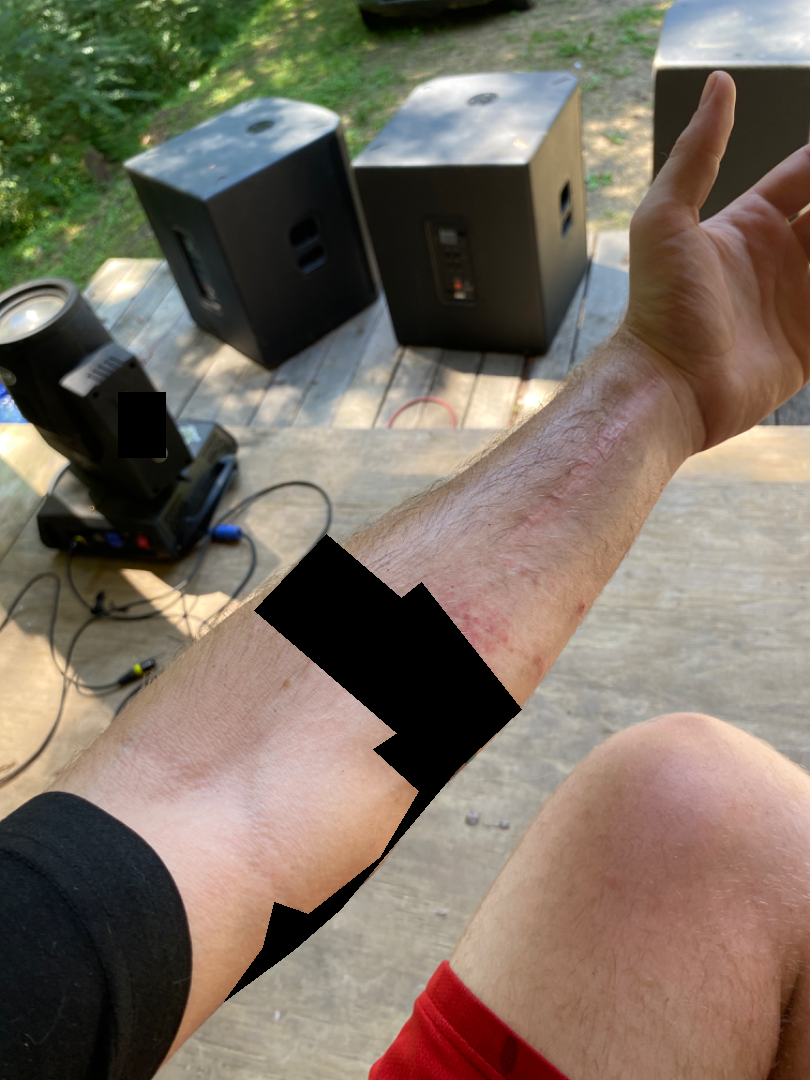| feature | finding |
|---|---|
| assessment | ungradable on photographic review |
| anatomic site | arm |
| photo taken | at a distance |